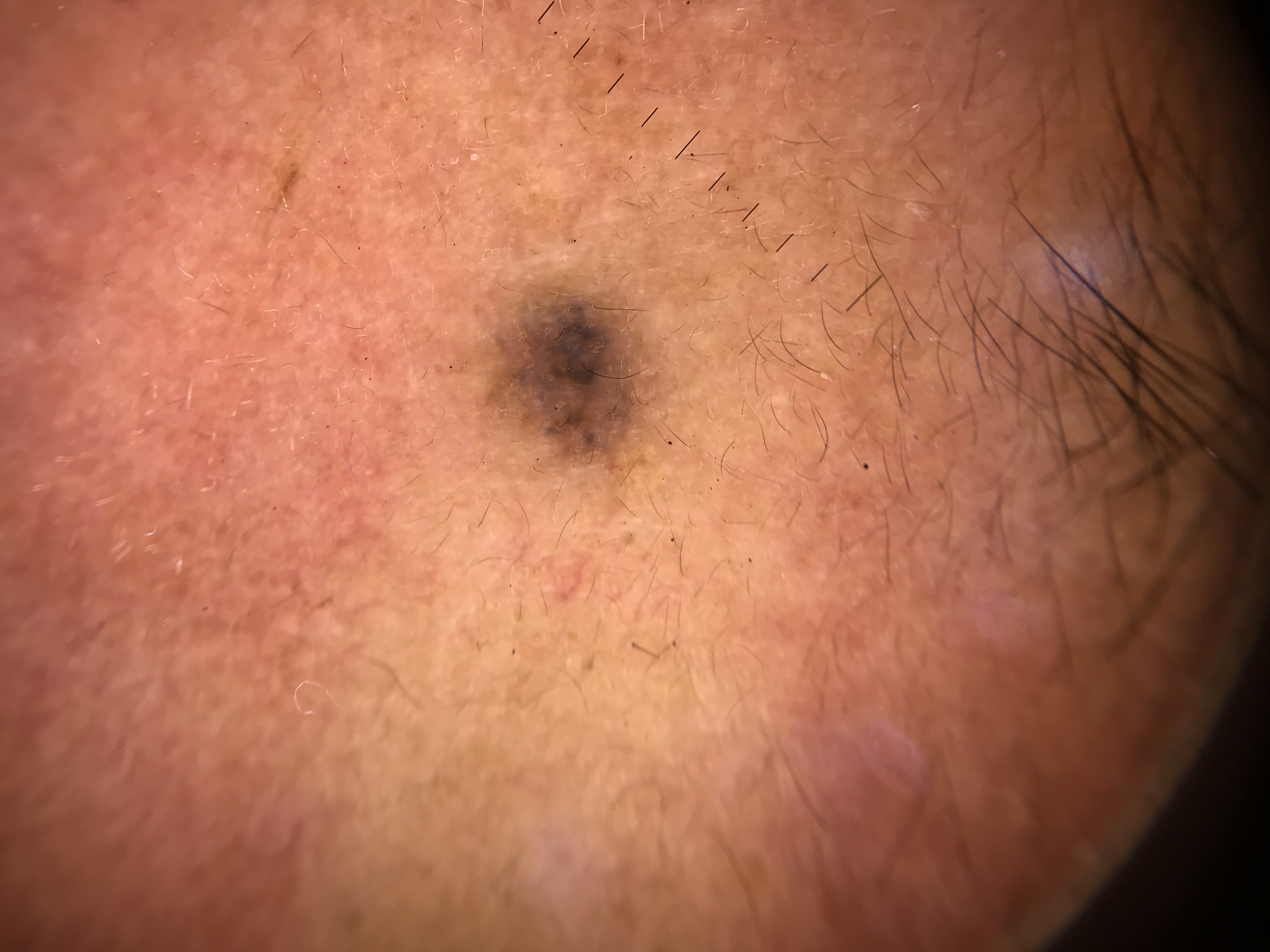A dermatoscopic image of a skin lesion.
The morphology is that of a keratinocytic lesion.
Biopsy-confirmed as a malignancy — a basal cell carcinoma.